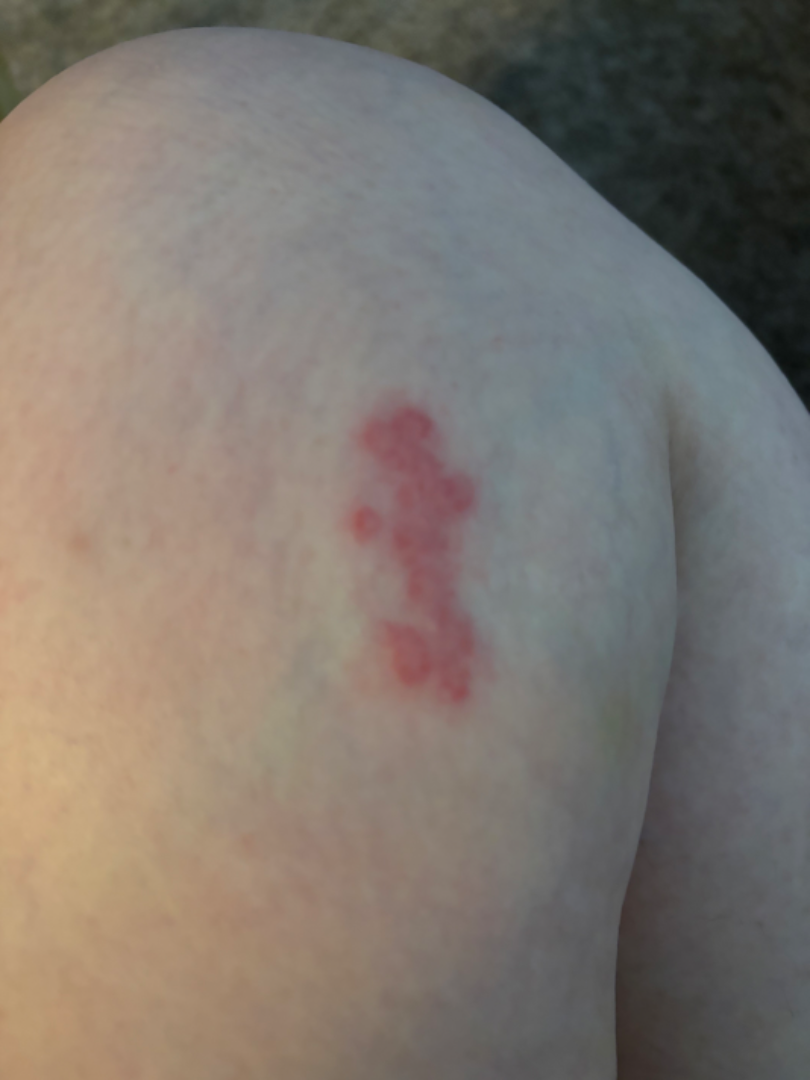assessment=indeterminate.